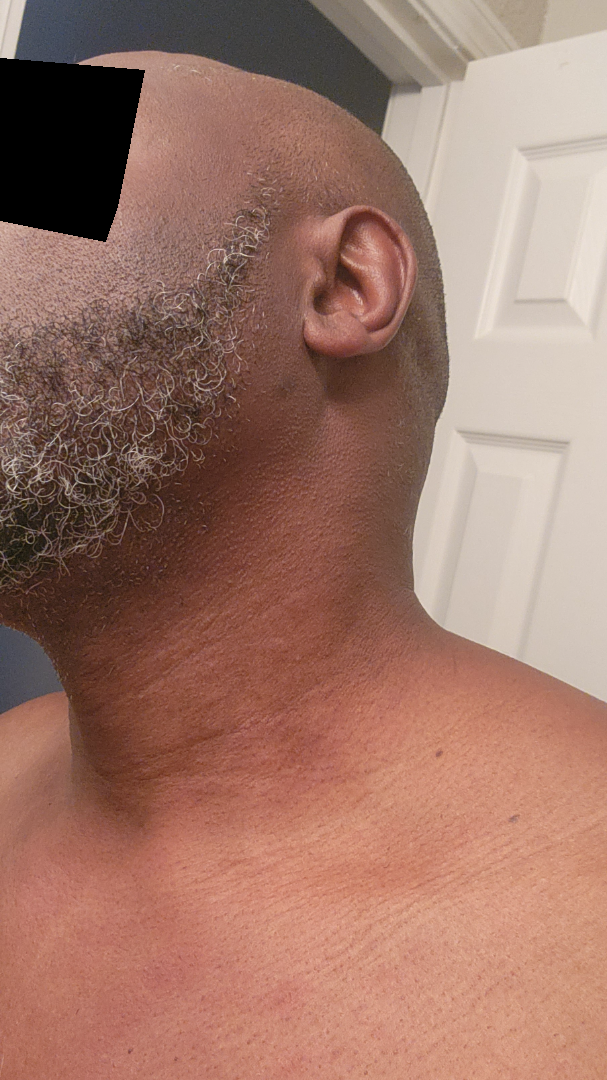Q: What is the framing?
A: close-up